A female subject aged 57; the patient was assessed as Fitzpatrick phototype III; by history, prior malignancy (patient or family), pesticide exposure, and prior skin cancer (patient or family); a smartphone photograph of a skin lesion:
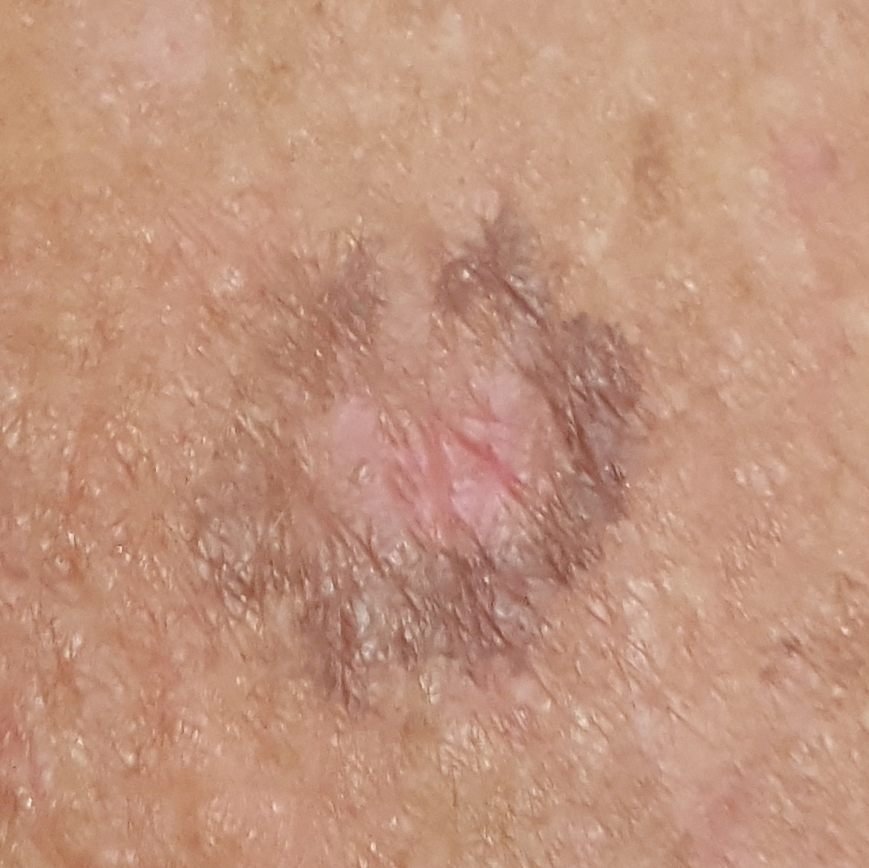anatomic site: the chest | diameter: 15 × 13 mm | symptoms: itching | diagnostic label: actinic keratosis (biopsy-proven).